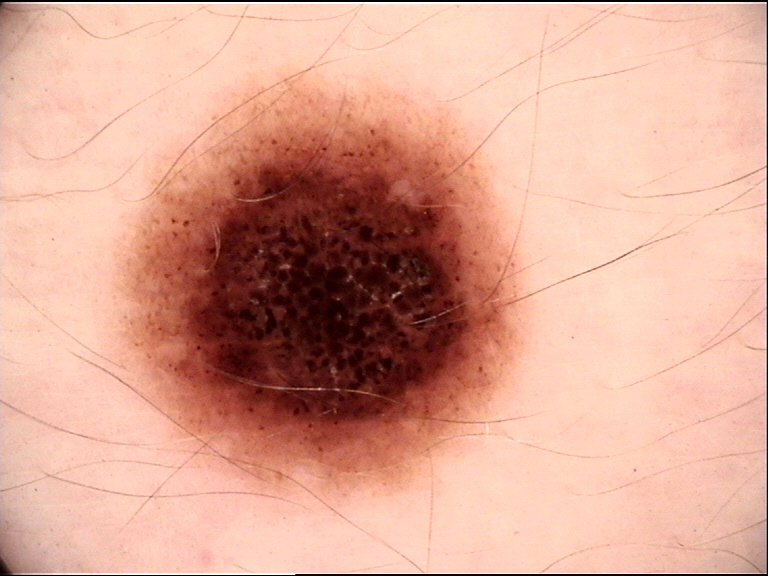Summary:
Dermoscopy of a skin lesion.
Impression:
The diagnosis was a dysplastic junctional nevus.